Dermoscopy of a skin lesion:
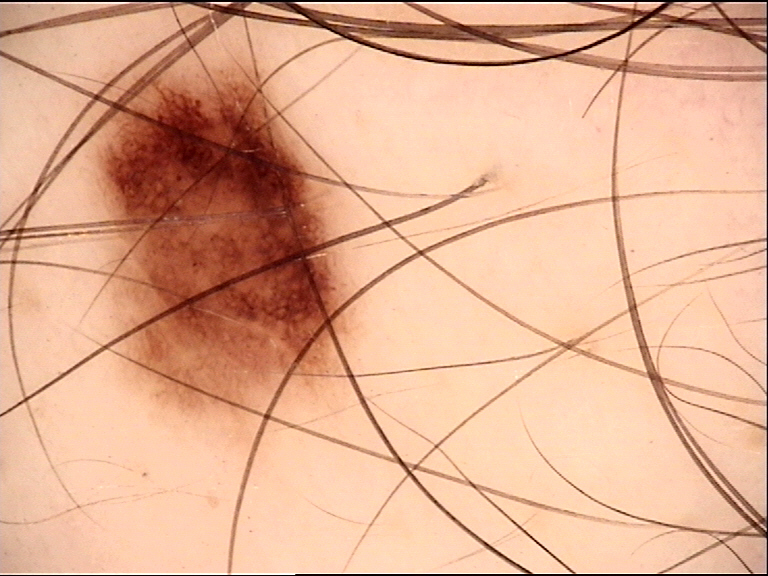Case:
- diagnostic label — dysplastic junctional nevus (expert consensus)